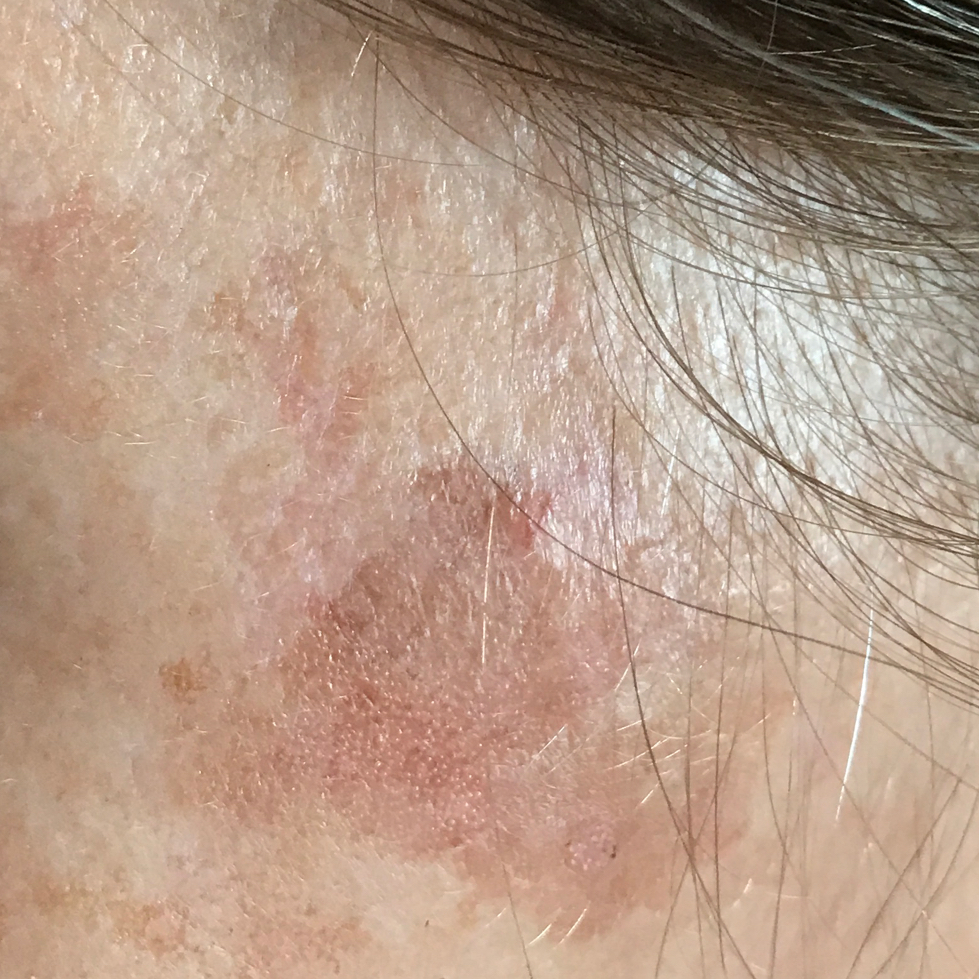imaging = clinical photograph; patient = in their 50s; region = the face; symptoms = itching, elevation; impression = actinic keratosis (clinical consensus).